A close-up photograph · the contributor is 18–29, female · the leg is involved: 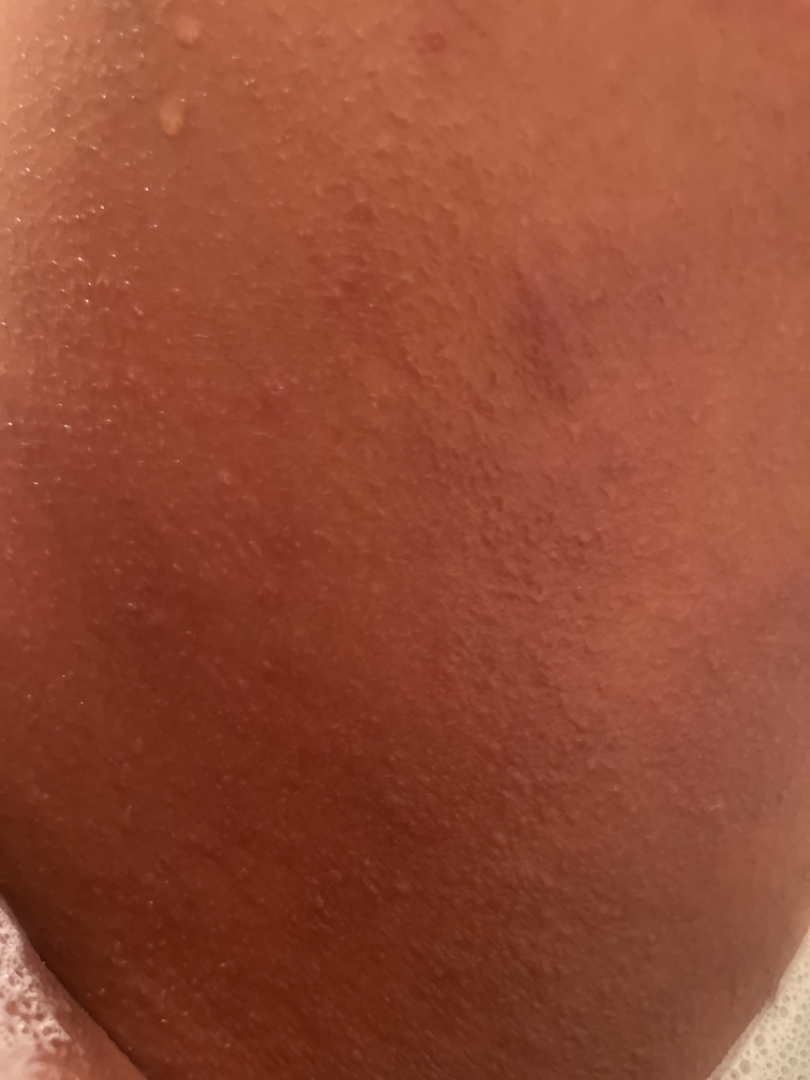differential=the reviewer's impression was Acute and chronic dermatitis.